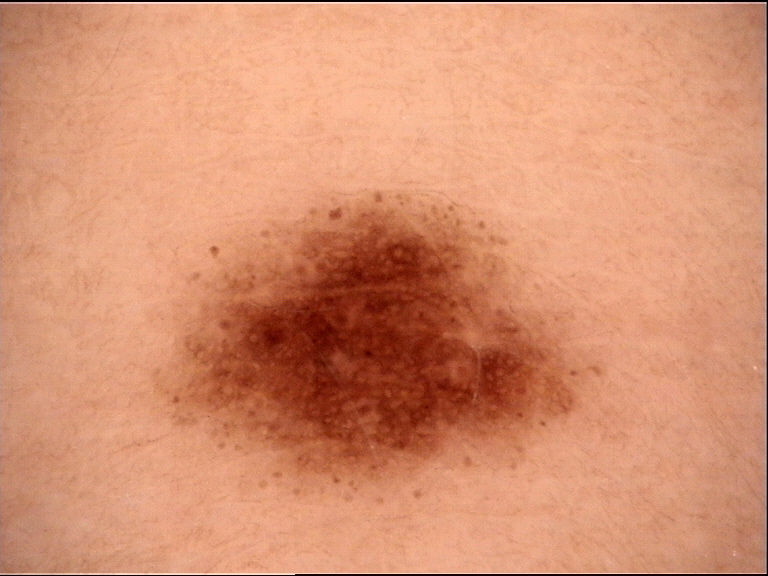Findings:
– diagnostic label · dysplastic junctional nevus (expert consensus)